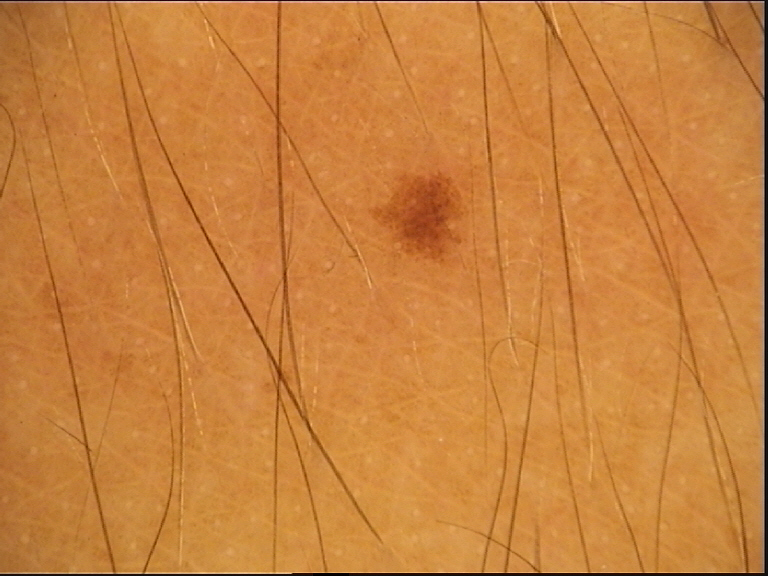A dermatoscopic image of a skin lesion. The diagnosis was a dysplastic junctional nevus.